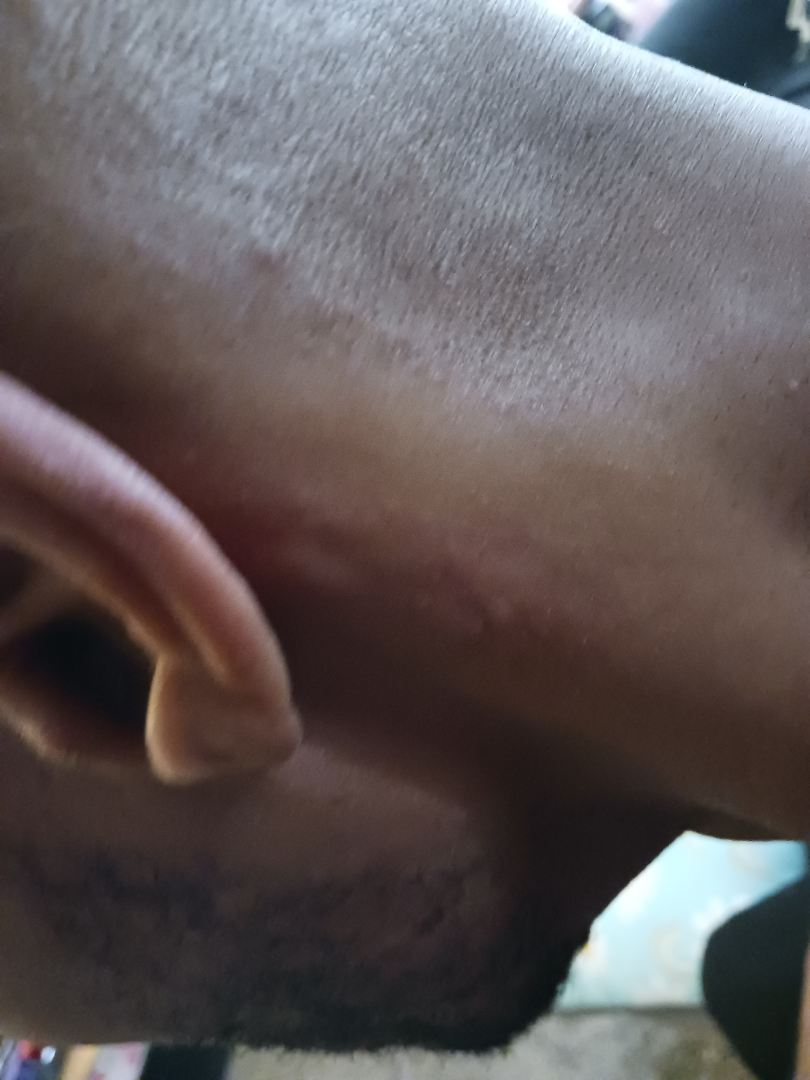assessment — unable to determine
image framing — at an angle